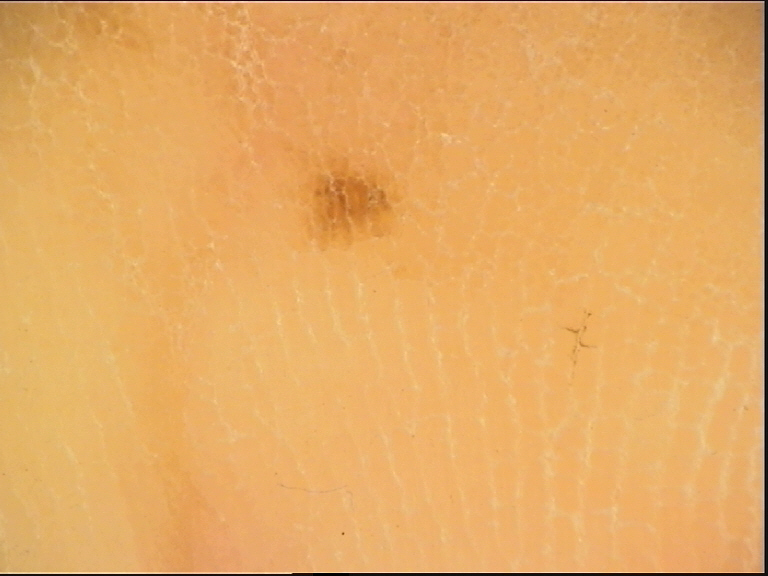A dermoscopic photograph of a skin lesion. The diagnosis was an acral dysplastic junctional nevus.